A dermoscopic view of a skin lesion: 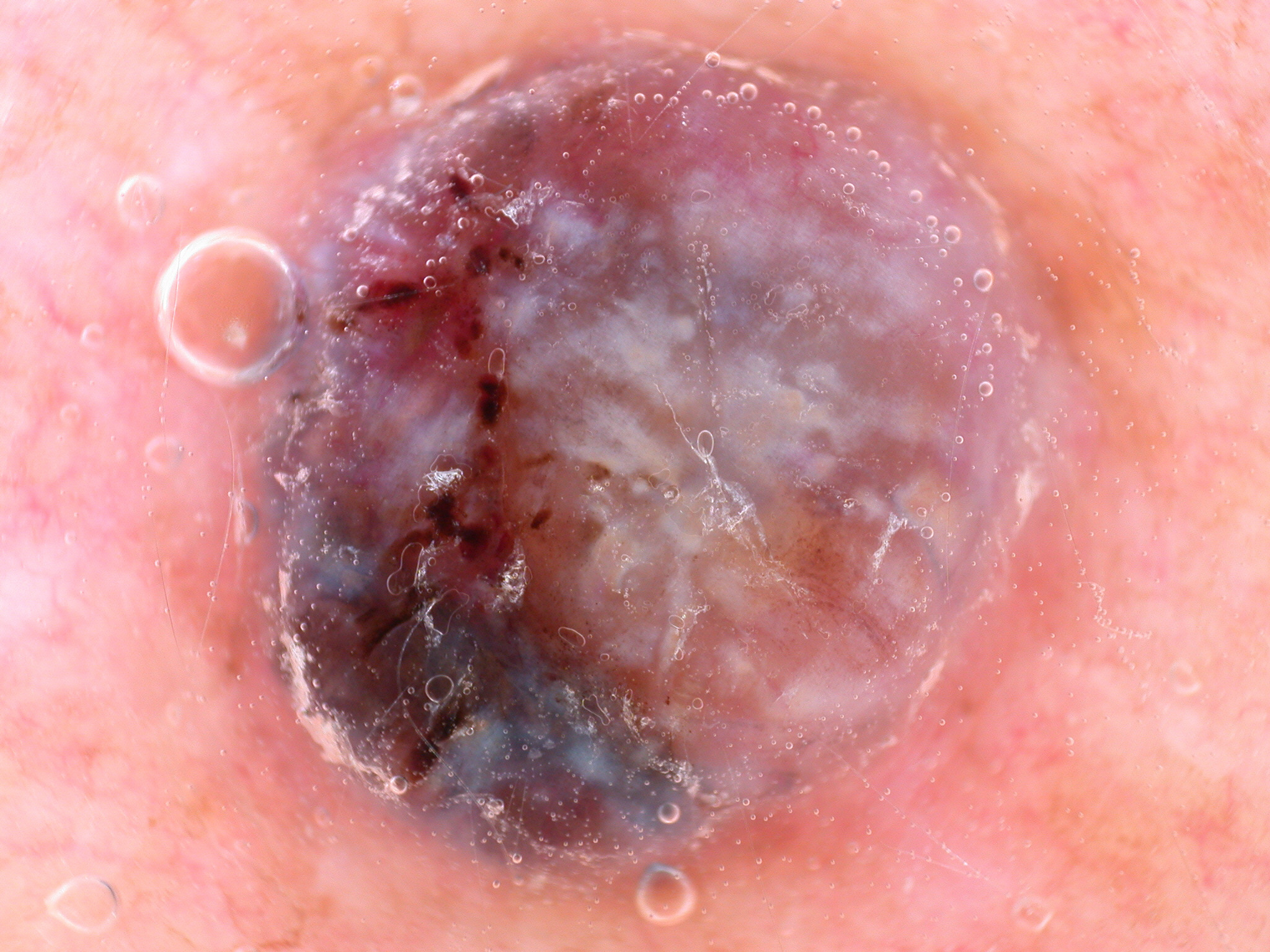bounding box: bbox(228, 32, 1103, 907) | dermoscopic pattern: globules | diagnosis: a melanoma, a skin cancer.